A dermoscopic close-up of a skin lesion.
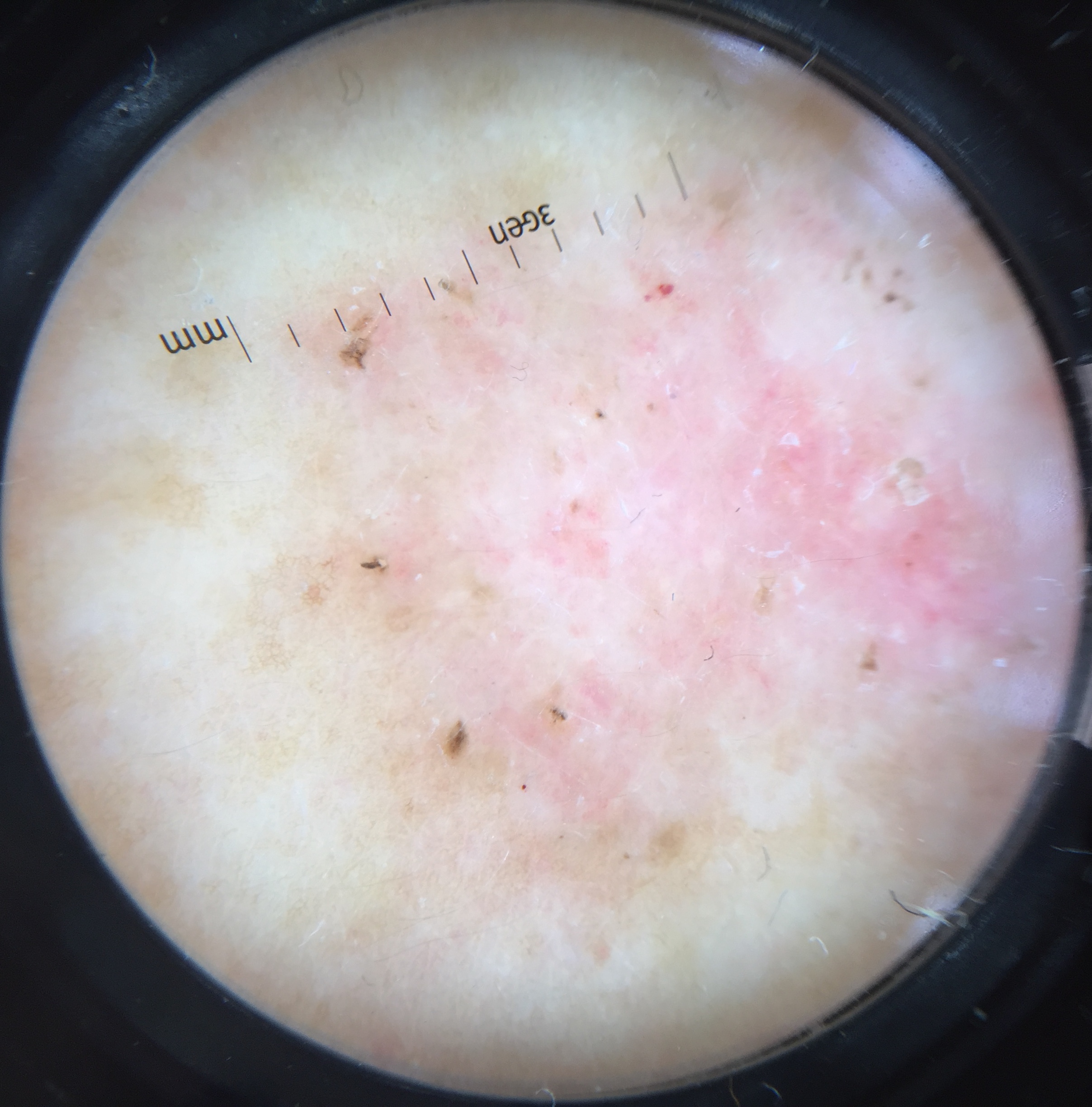Case:
- classification — keratinocytic
- label — basal cell carcinoma (biopsy-proven)